This is a dermoscopic photograph of a skin lesion, the subject is a female roughly 50 years of age: 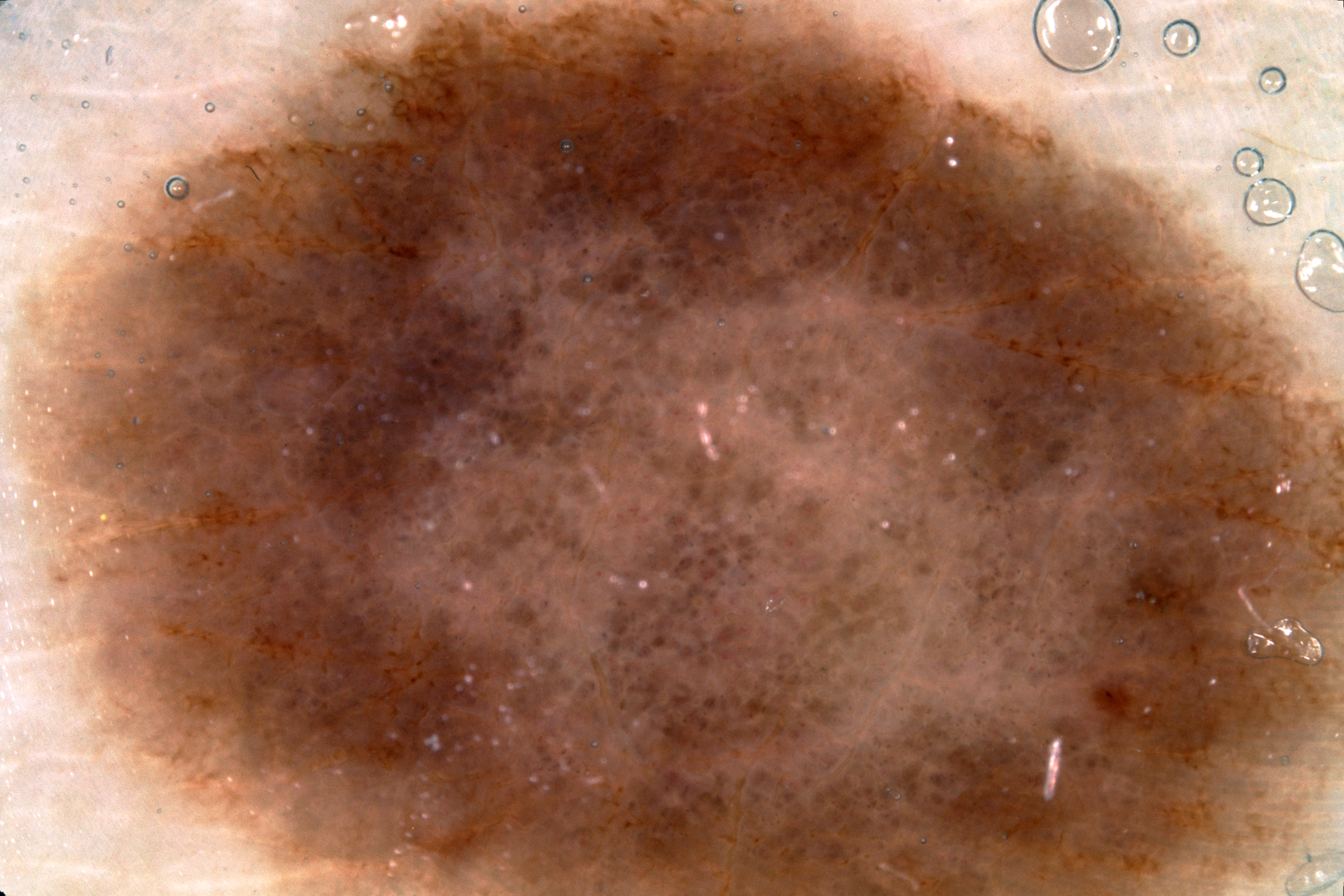dermoscopic_features:
  present:
    - negative network
    - pigment network
  absent:
    - milia-like cysts
    - streaks
lesion_location: spans the dermoscopic field
diagnosis:
  name: melanocytic nevus
  malignancy: benign
  lineage: melanocytic
  provenance: clinical